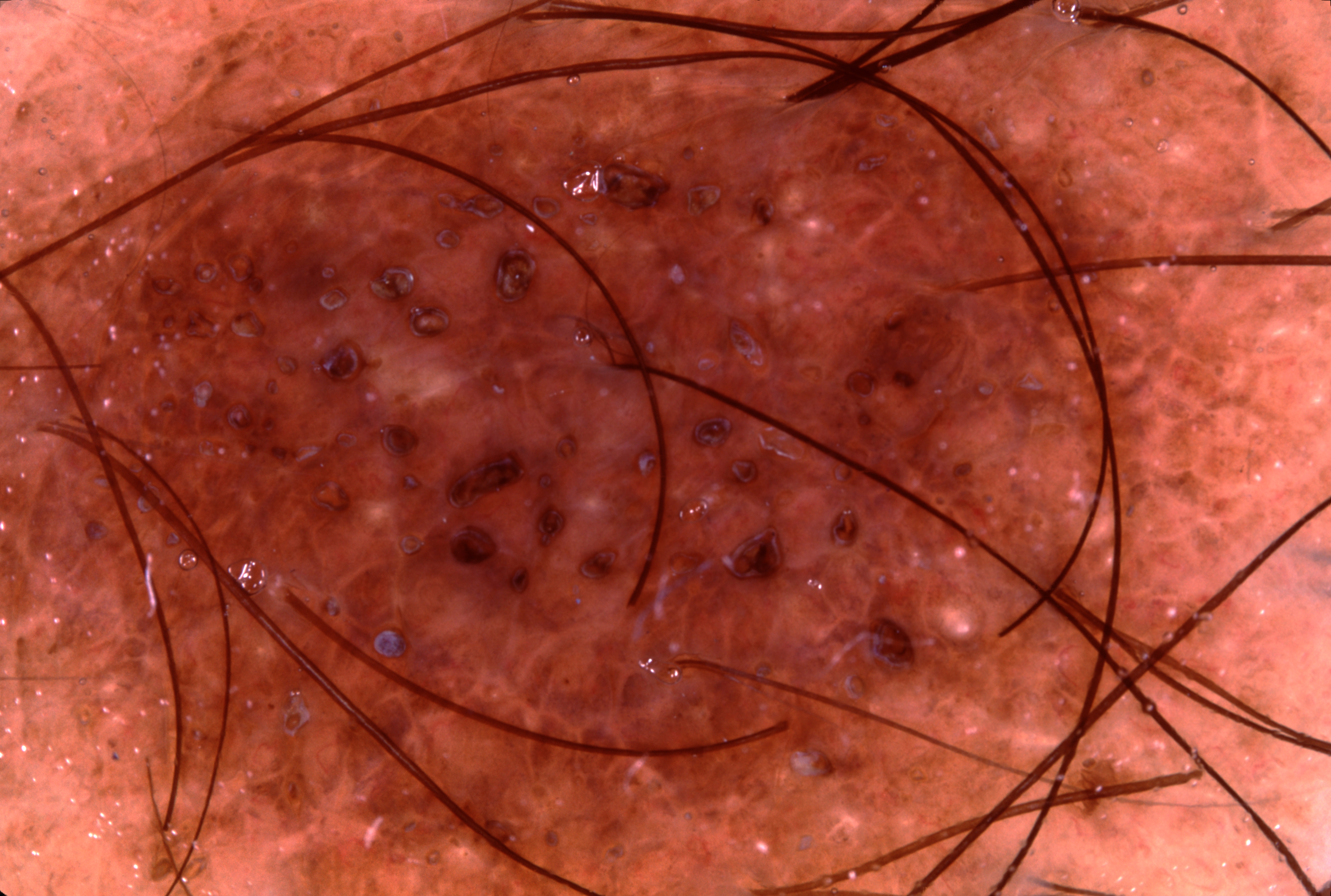imaging = dermoscopic image, dermoscopic features = milia-like cysts, lesion extent = spans the dermoscopic field, diagnosis = a melanocytic nevus.